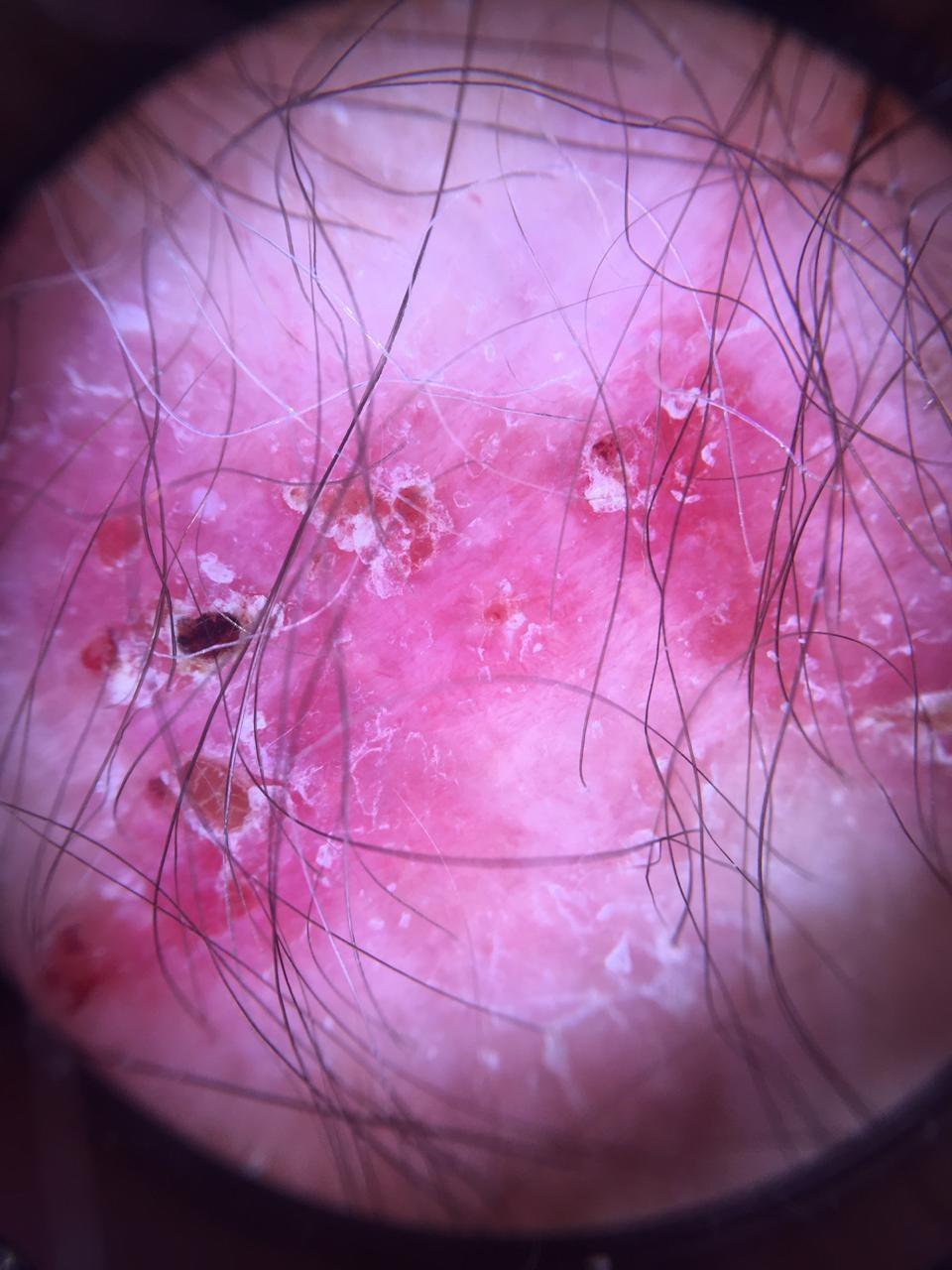imaging: dermatoscopic image; subject: male, aged approximately 85 or older; location: an upper extremity; diagnosis: Solar or actinic keratosis (biopsy-proven).